The contributor reports the lesion is raised or bumpy. Located on the top or side of the foot. The patient described the issue as a rash. No associated systemic symptoms reported. Reported duration is about one day. The photograph is a close-up of the affected area. The patient is a female aged 18–29. Reported lesion symptoms include itching and bothersome appearance — 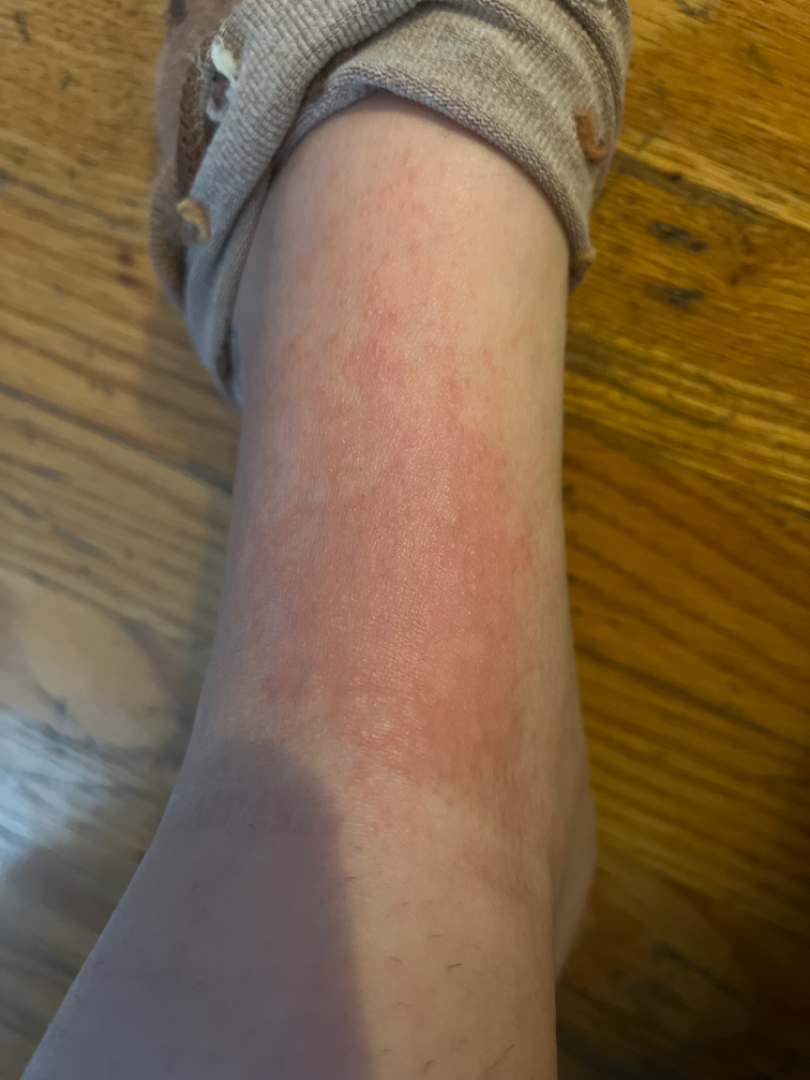On dermatologist assessment of the image, favoring Allergic Contact Dermatitis; with consideration of Irritant Contact Dermatitis; lower on the differential is Stasis Dermatitis.